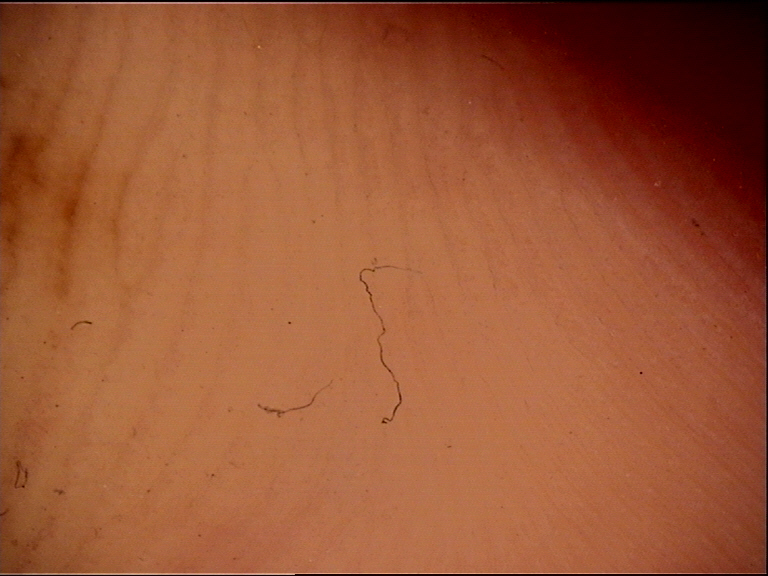| field | value |
|---|---|
| diagnostic label | acral junctional nevus (expert consensus) |